A dermoscopic close-up of a skin lesion:
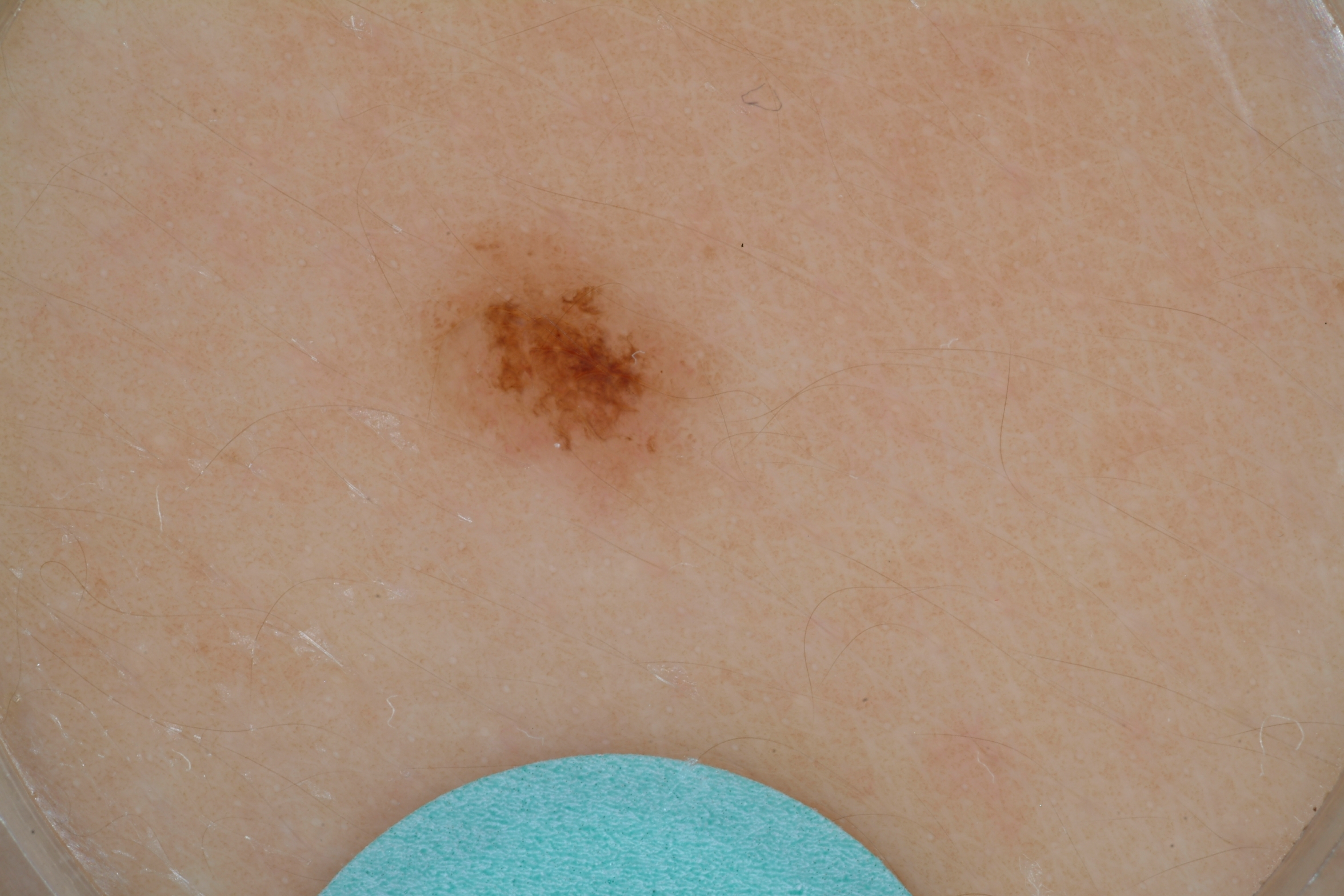Q: Which assessed dermoscopic features were absent?
A: streaks and globules
Q: How large is the lesion within the image?
A: small
Q: Where is the lesion located?
A: left=392, top=206, right=727, bottom=513
Q: What is this lesion?
A: a benign lesion